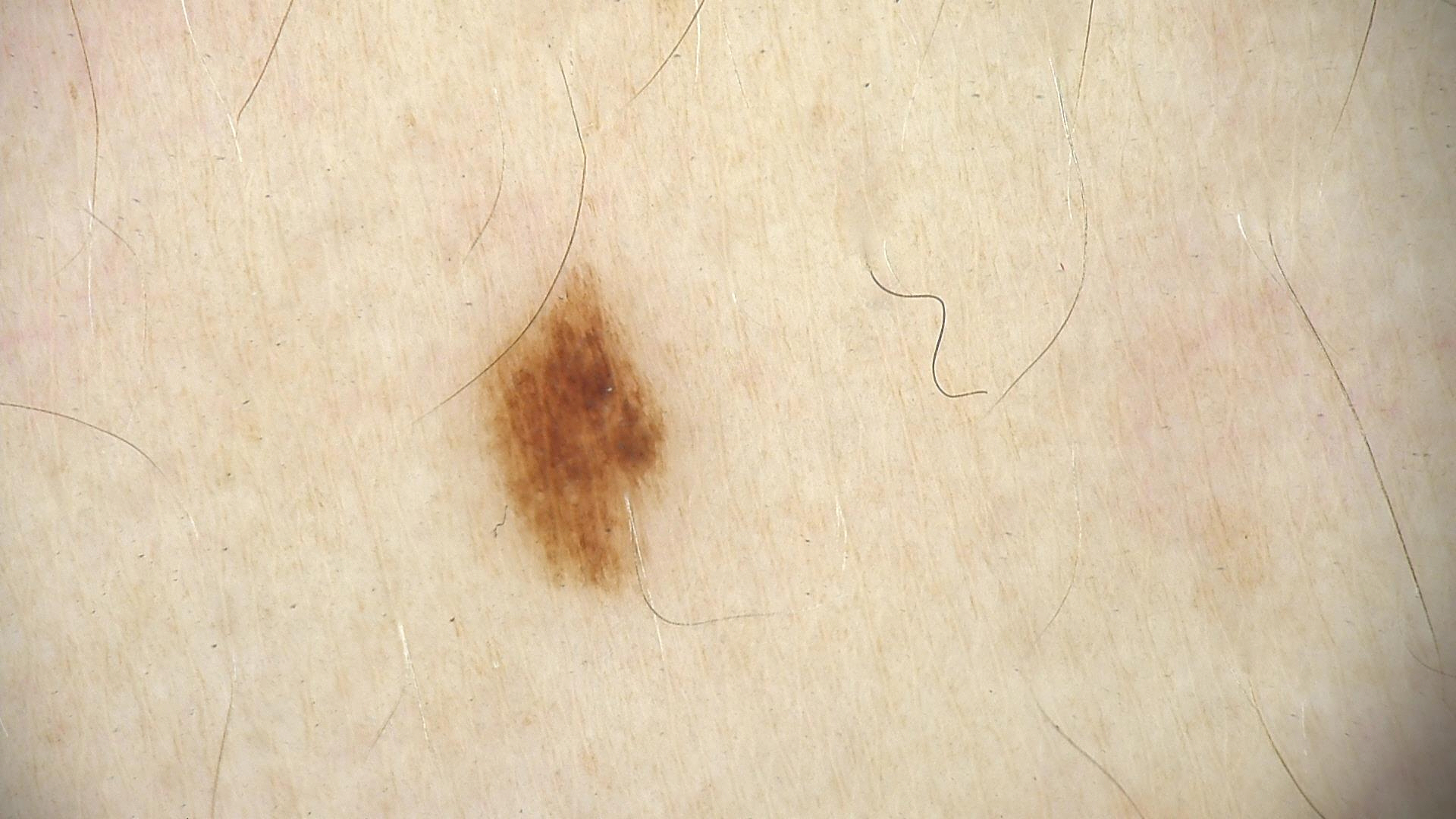The diagnosis was a banal lesion — a junctional nevus.